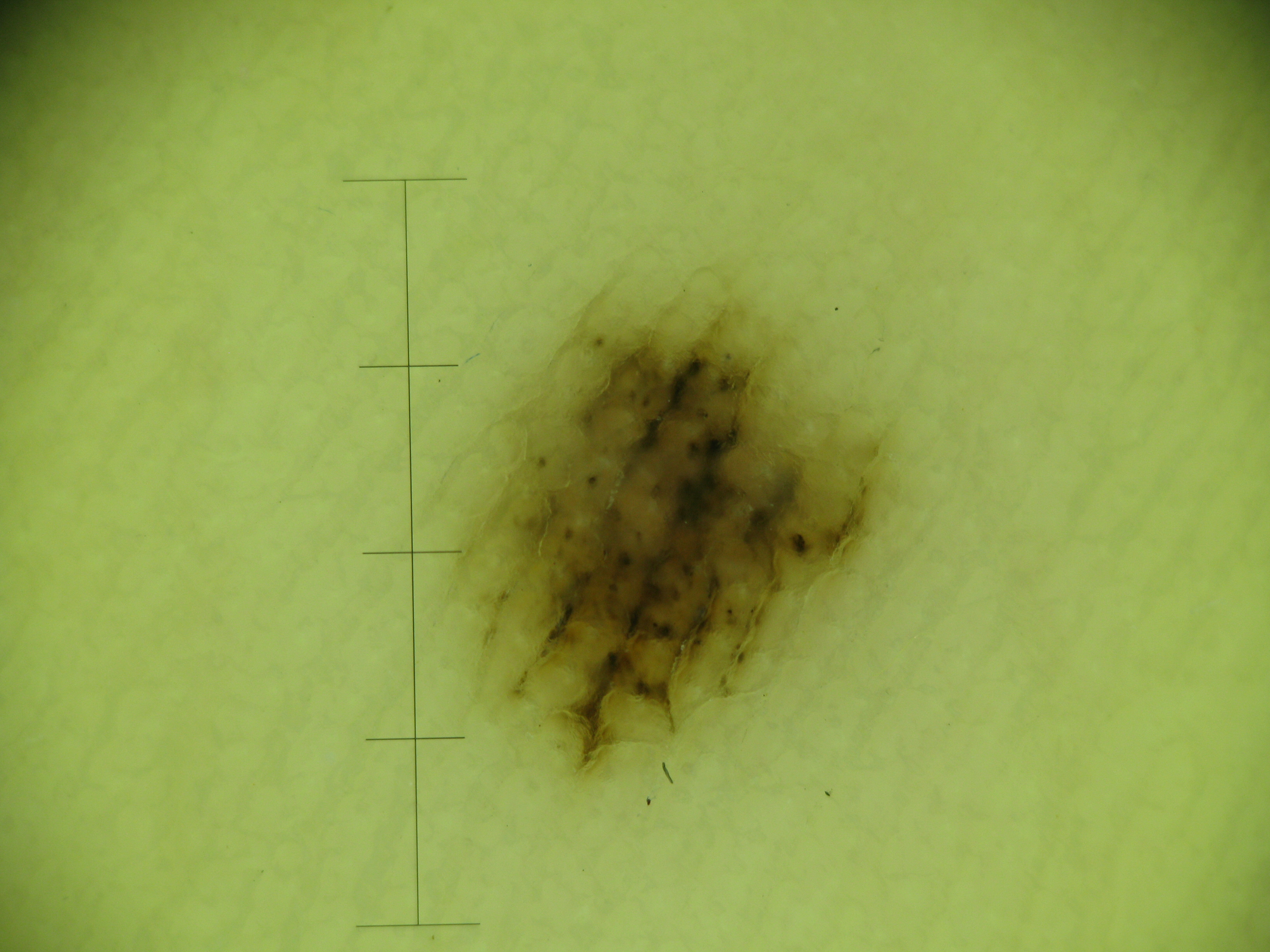diagnosis = acral compound nevus (expert consensus).